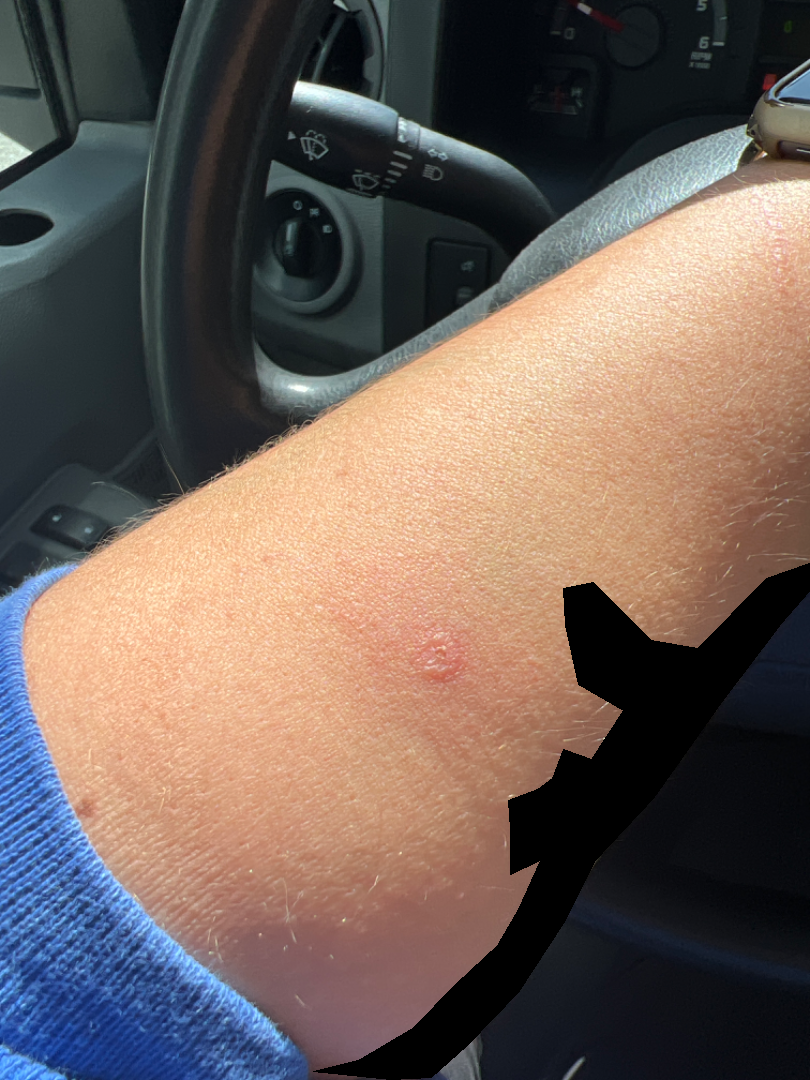Clinical context: The patient is a female aged 30–39. Close-up view. The lesion involves the arm. Assessment: Insect Bite (primary); Contact burn of skin (possible); Allergic Contact Dermatitis (possible).